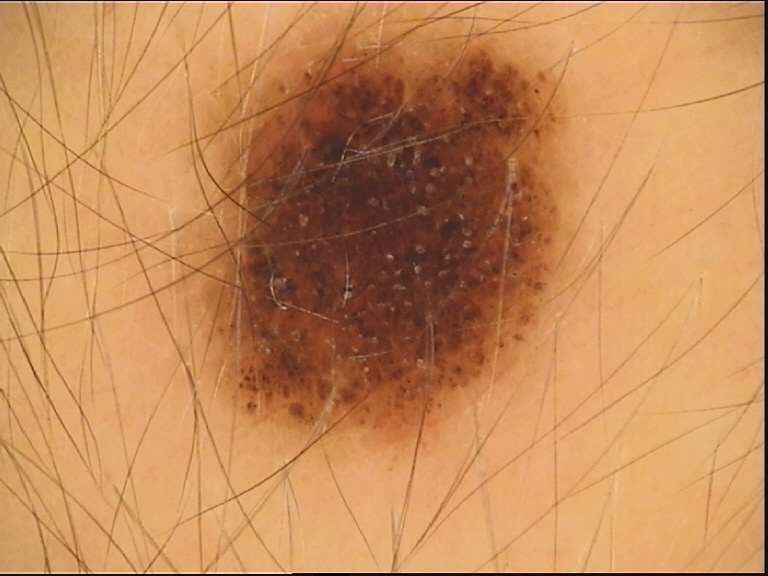Conclusion:
Classified as a compound nevus.